The affected area is the leg; the photograph was taken at an angle; female patient, age 30–39.
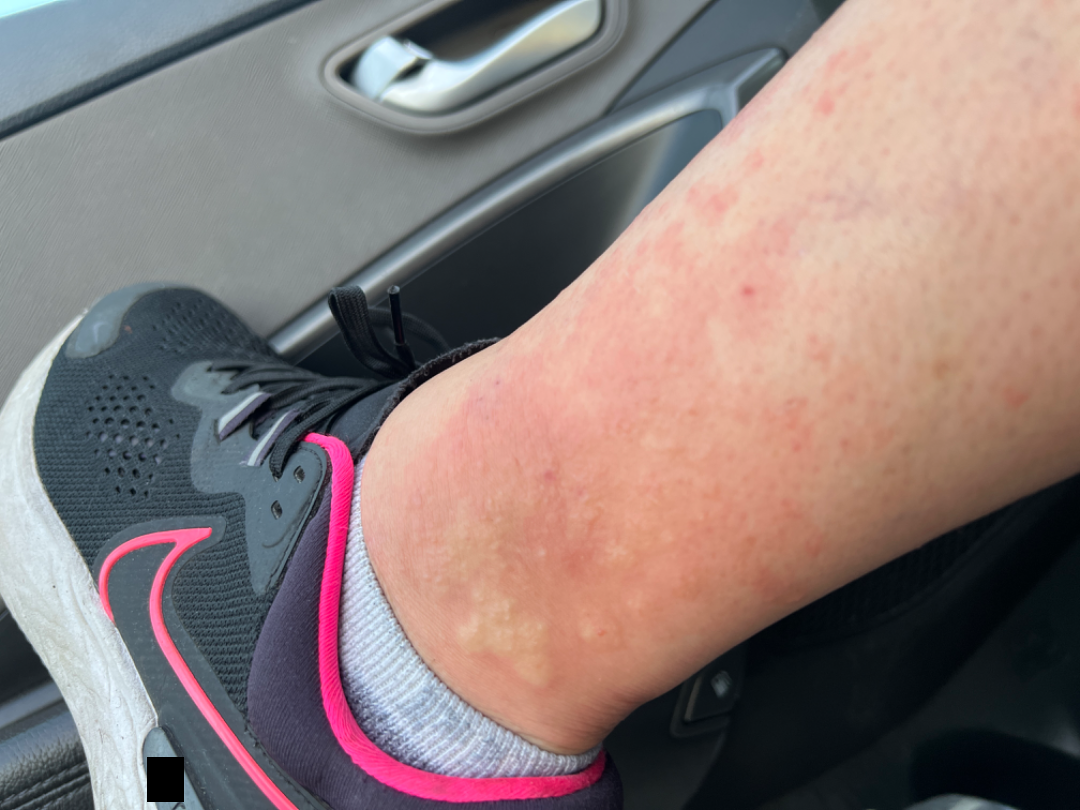The lesion is associated with bothersome appearance and itching.
Self-categorized by the patient as a rash.
Texture is reported as raised or bumpy.
The condition has been present for less than one week.
Reviewed remotely by one dermatologist: favoring Eczema; an alternative is Psoriasis.